The contributor is a male aged 30–39 · the photograph is a close-up of the affected area · the lesion involves the arm, back of the hand, top or side of the foot and leg.
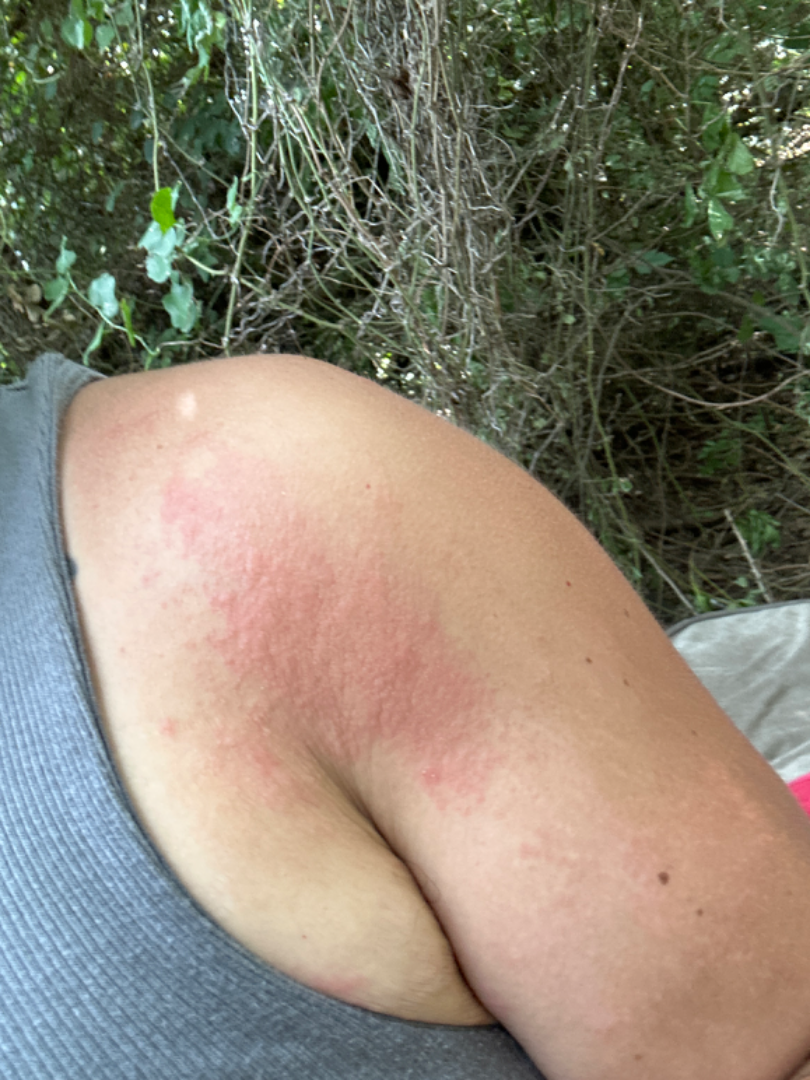| key | value |
|---|---|
| associated systemic symptoms | none reported |
| duration | less than one week |
| patient's own categorization | a rash |
| reported symptoms | itching, darkening and burning |
| dermatologist impression | the differential is split between Acute dermatitis, NOS and Allergic Contact Dermatitis |